A dermoscopic image of a skin lesion.
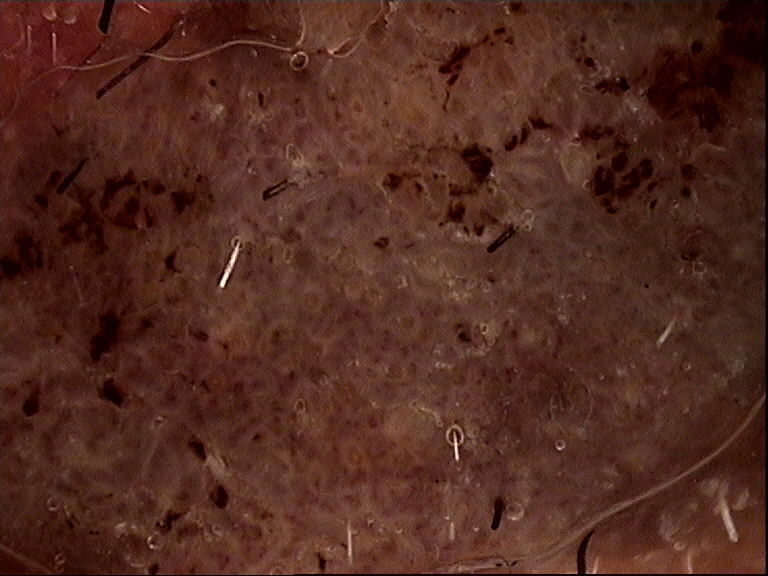Q: What is the lesion category?
A: keratinocytic
Q: What is this lesion?
A: seborrheic keratosis (expert consensus)